A skin lesion imaged with a dermatoscope.
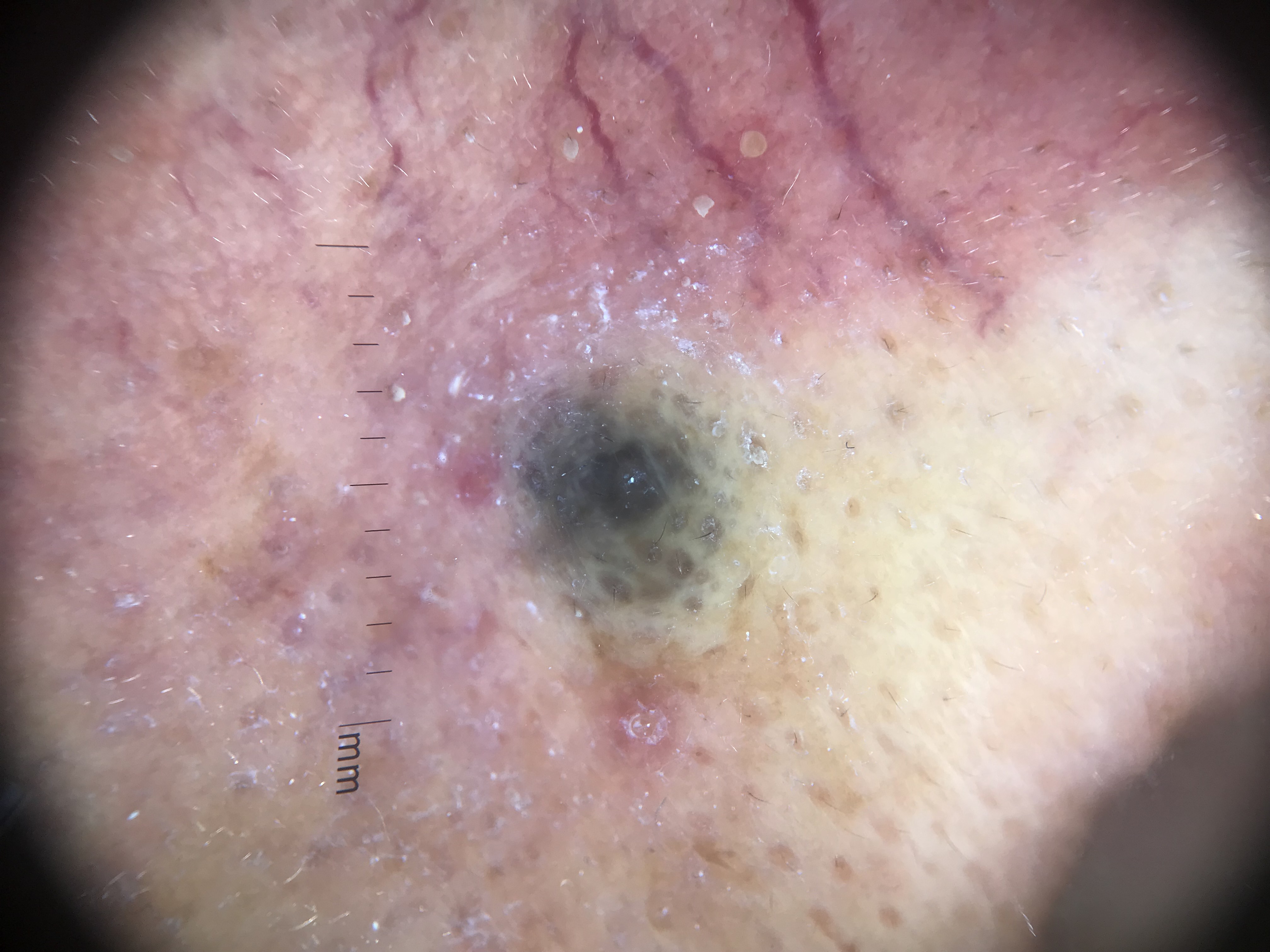The architecture is that of a dermal, banal lesion.
Consistent with a blue nevus.